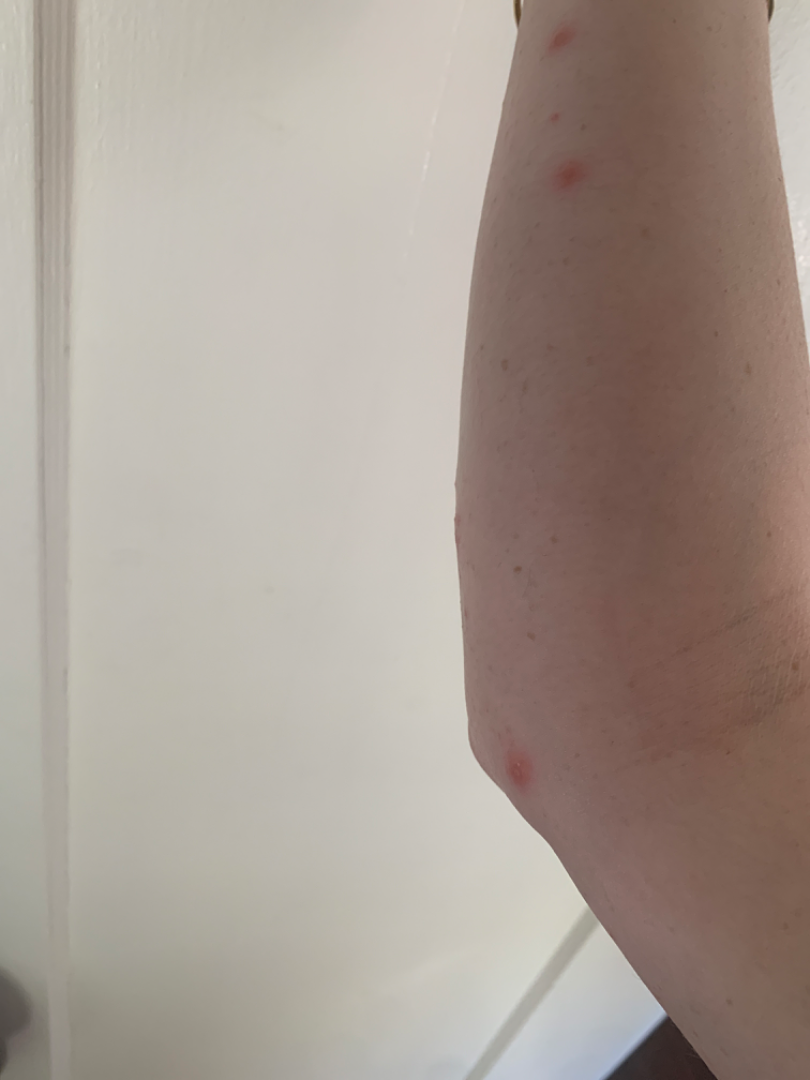• framing: at a distance
• anatomic site: arm
• differential diagnosis: most likely Insect Bite